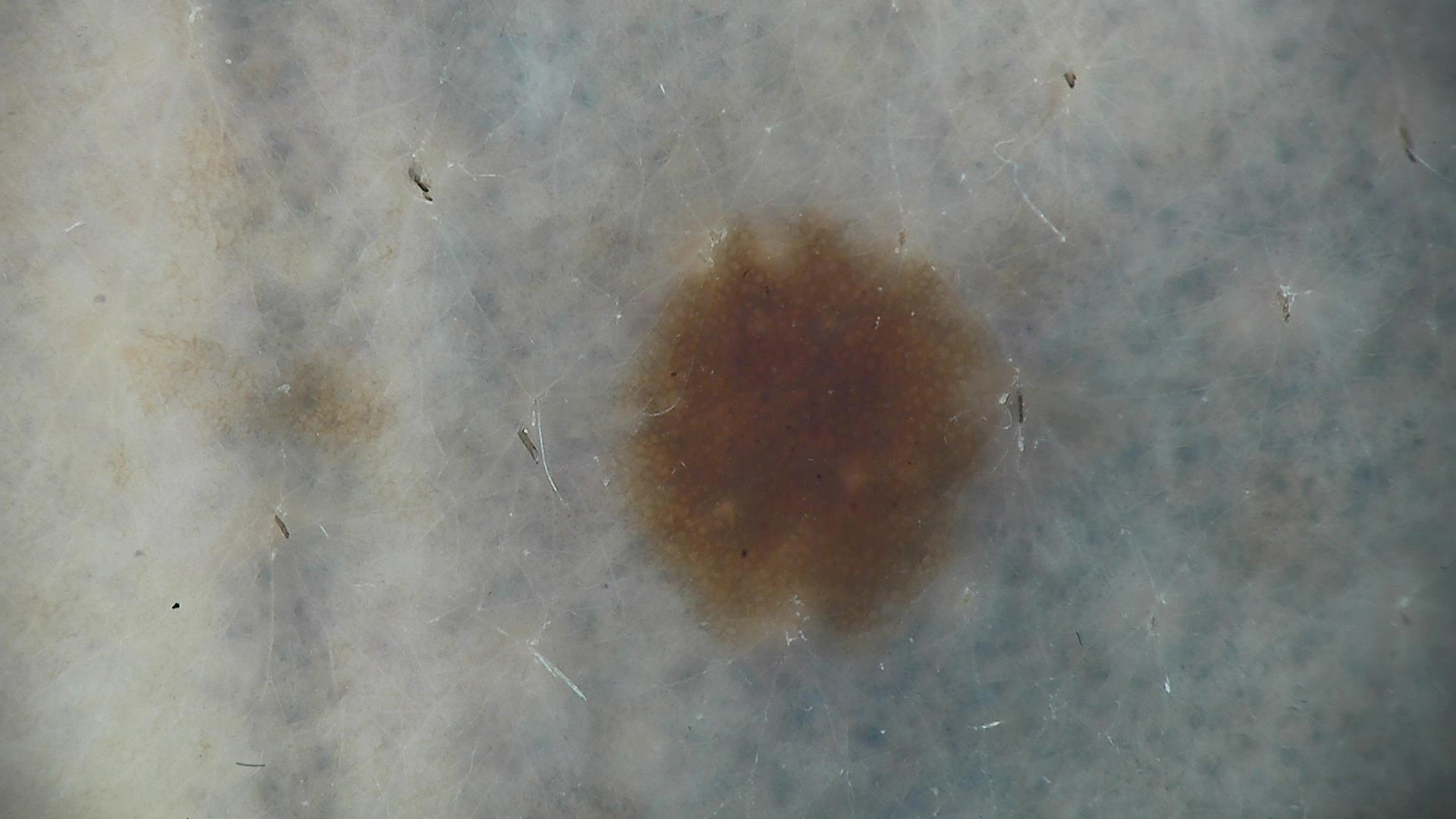image type = dermoscopy | assessment = dysplastic junctional nevus (expert consensus).